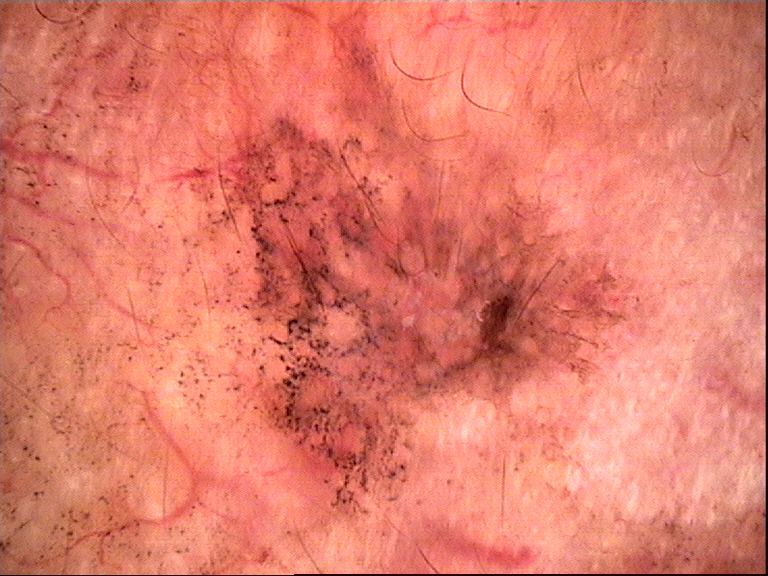Diagnosed as a lichenoid keratosis.